Dermoscopy of a skin lesion:
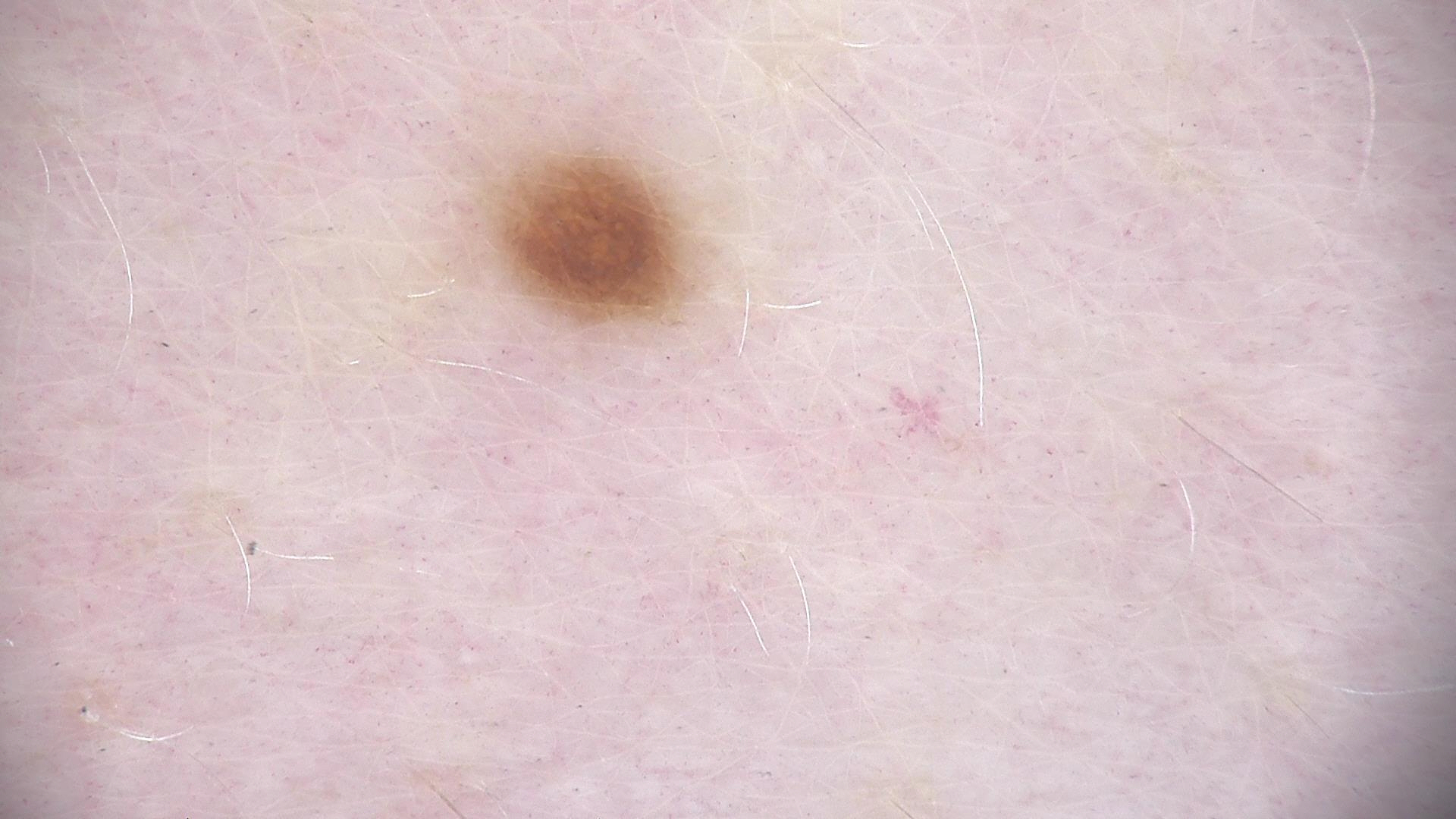diagnostic label=dysplastic junctional nevus (expert consensus)